A male patient age 76; a macroscopic clinical photograph of a skin lesion; the referring clinician suspected basal cell carcinoma:
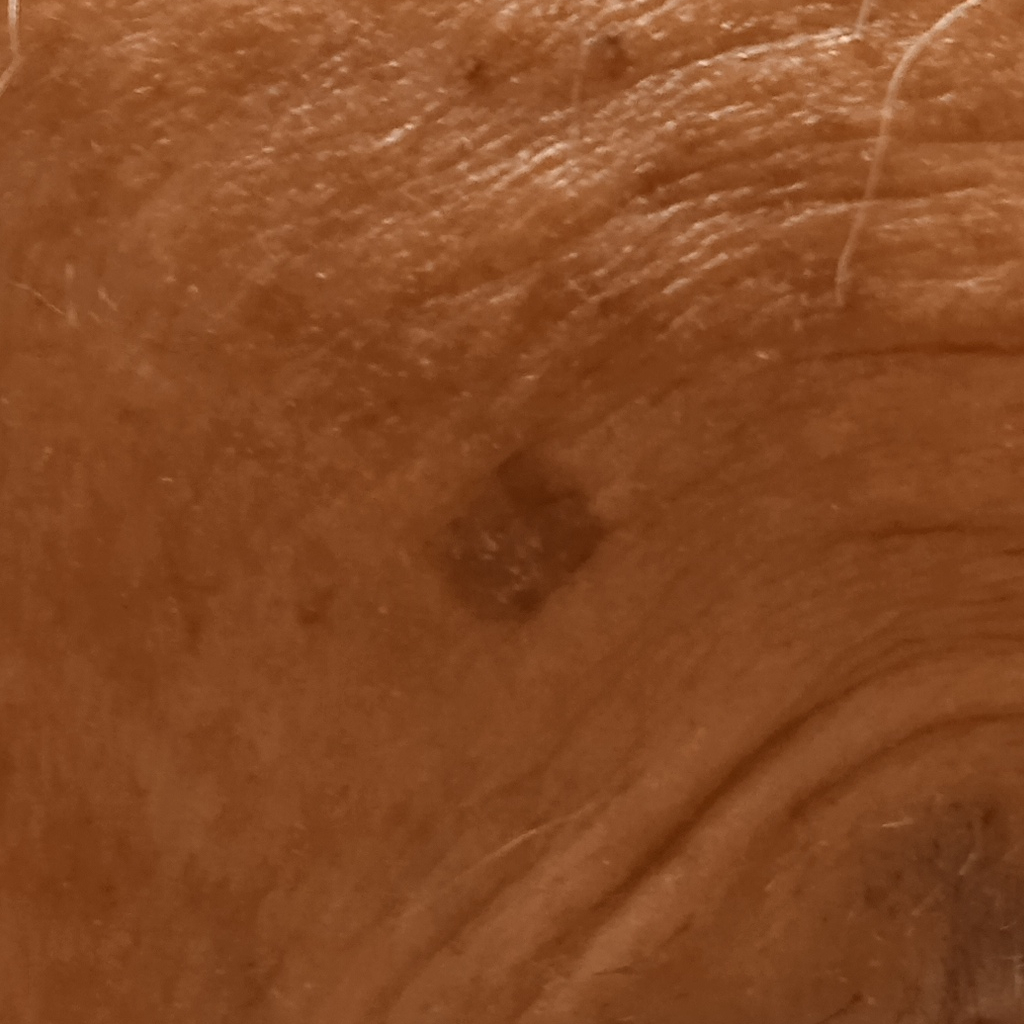Findings:
• anatomic site — the face
• lesion size — 8.7 mm
• diagnosis — basal cell carcinoma (biopsy-proven)